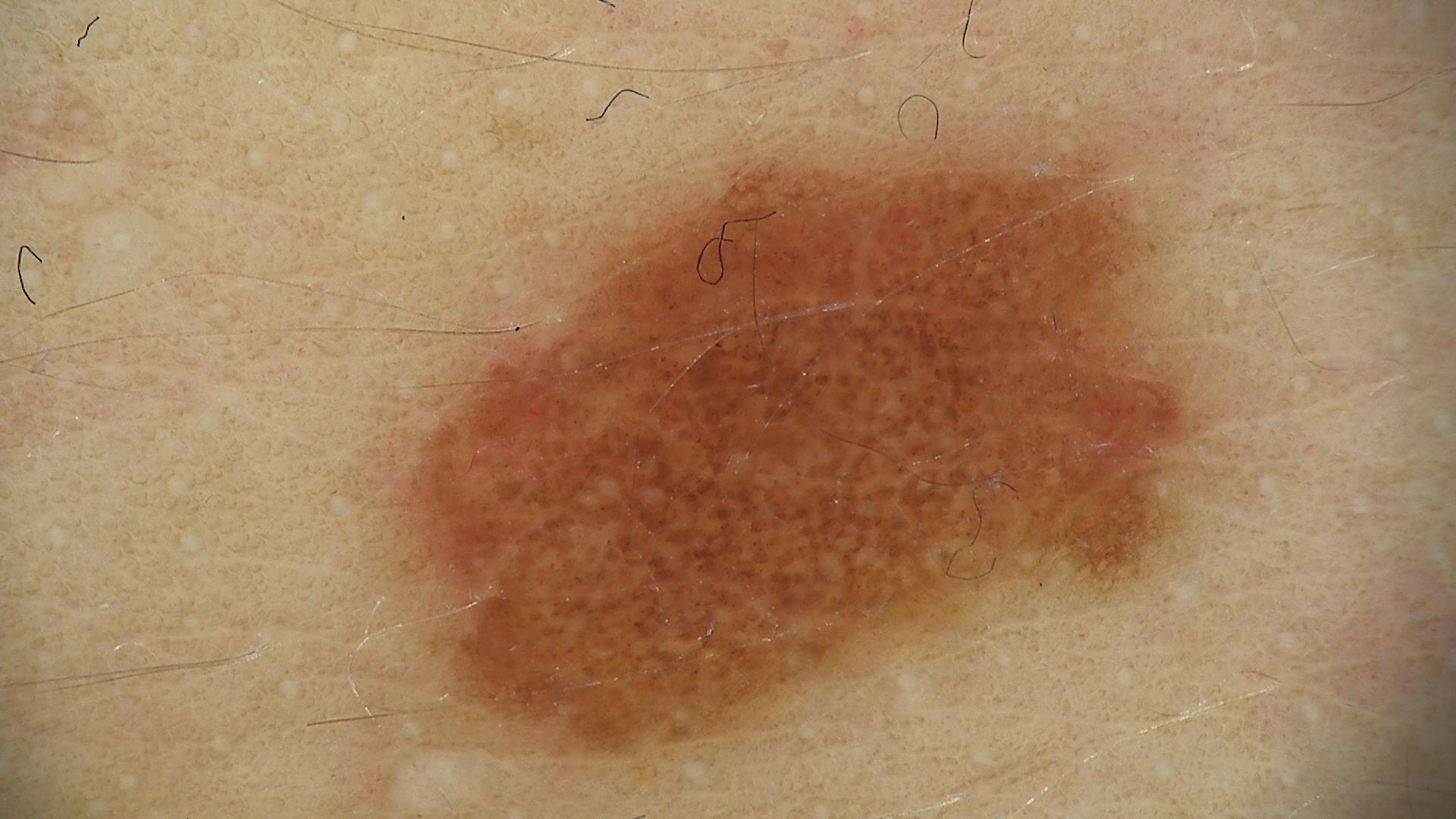diagnosis: dysplastic junctional nevus (expert consensus).